A dermoscopy image of a single skin lesion:
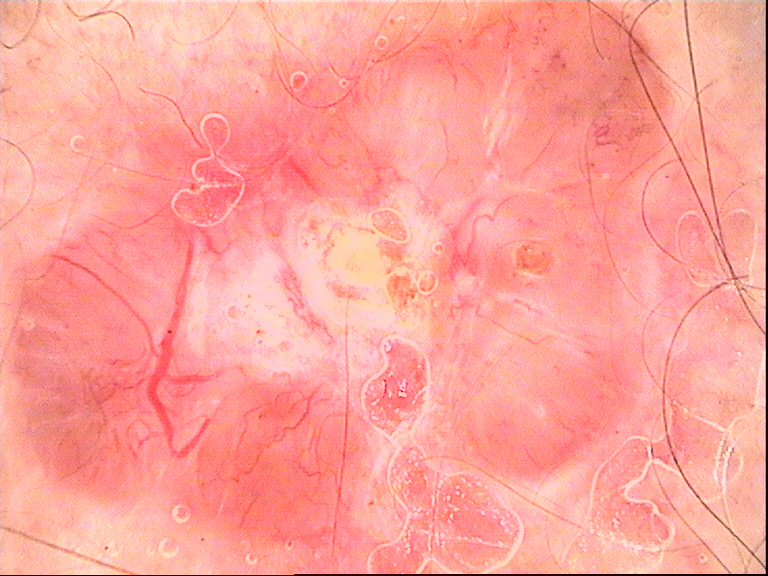Pathology:
The biopsy diagnosis was a basal cell carcinoma.